The photograph was taken at a distance.
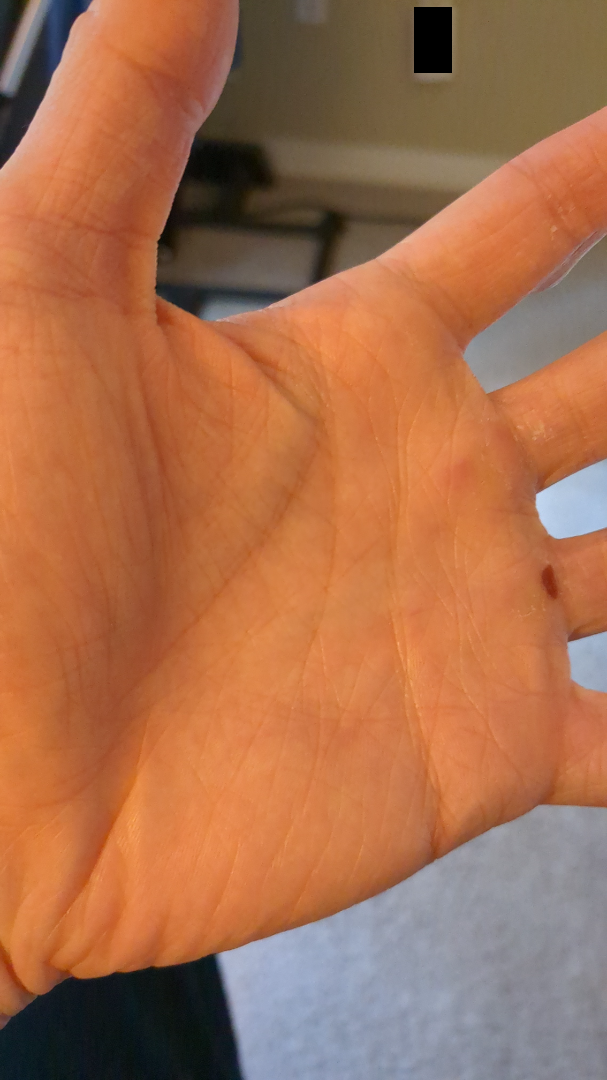Impression:
The skin findings could not be characterized from the image.